A dermoscopic view of a skin lesion · a male subject, aged approximately 55 — 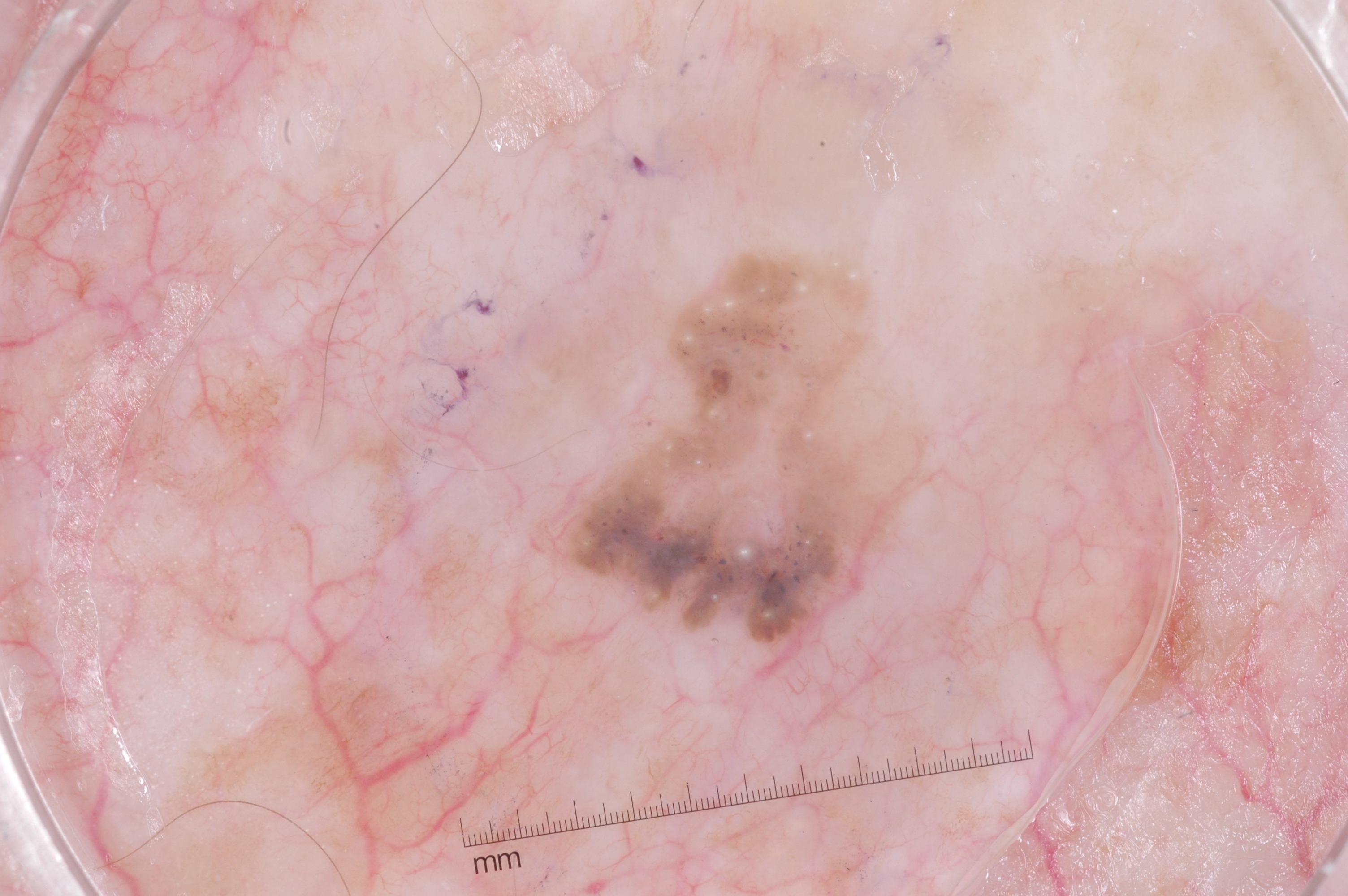Findings:
- dermoscopic findings — milia-like cysts; absent: streaks, negative network, and pigment network
- extent — moderate
- lesion bbox — 565/243/938/653
- diagnosis — a seborrheic keratosis